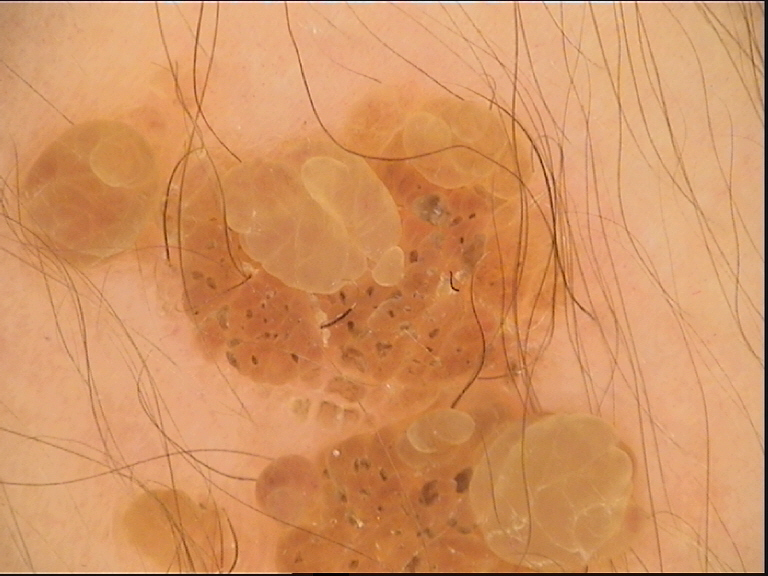The morphology is that of a keratinocytic lesion.
The diagnostic label was a benign lesion — a seborrheic keratosis.